Dermoscopy of a skin lesion; the subject is a female approximately 55 years of age: 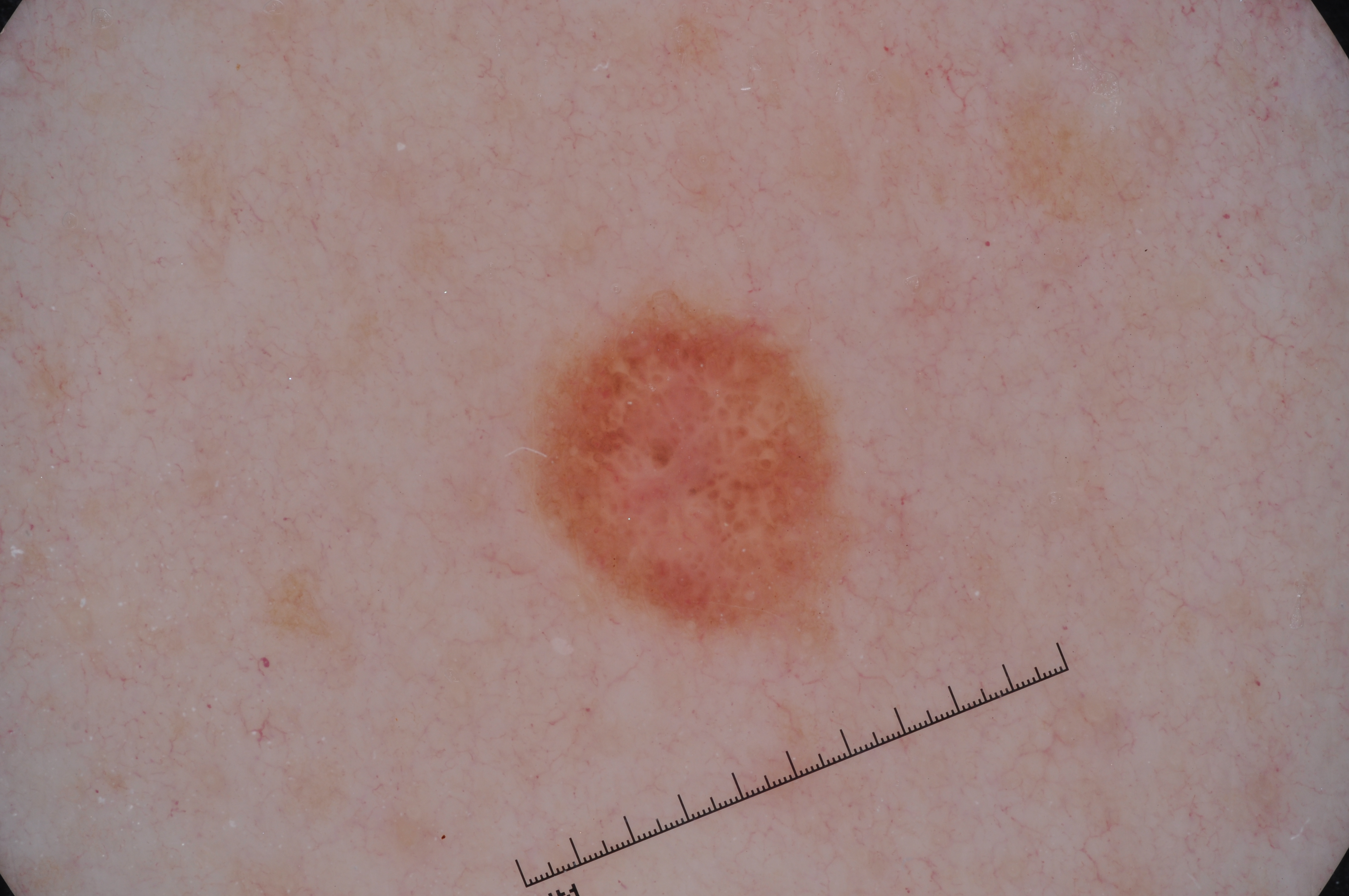lesion size = ~7% of the field
bounding box = 527/294/854/637
features = milia-like cysts, pigment network, and negative network
impression = a melanoma, a skin cancer